Reported lesion symptoms include bothersome appearance; the patient considered this a rash; the leg is involved; no relevant systemic symptoms; the subject is 18–29, female; this image was taken at an angle; the patient reports the condition has been present for about one day — 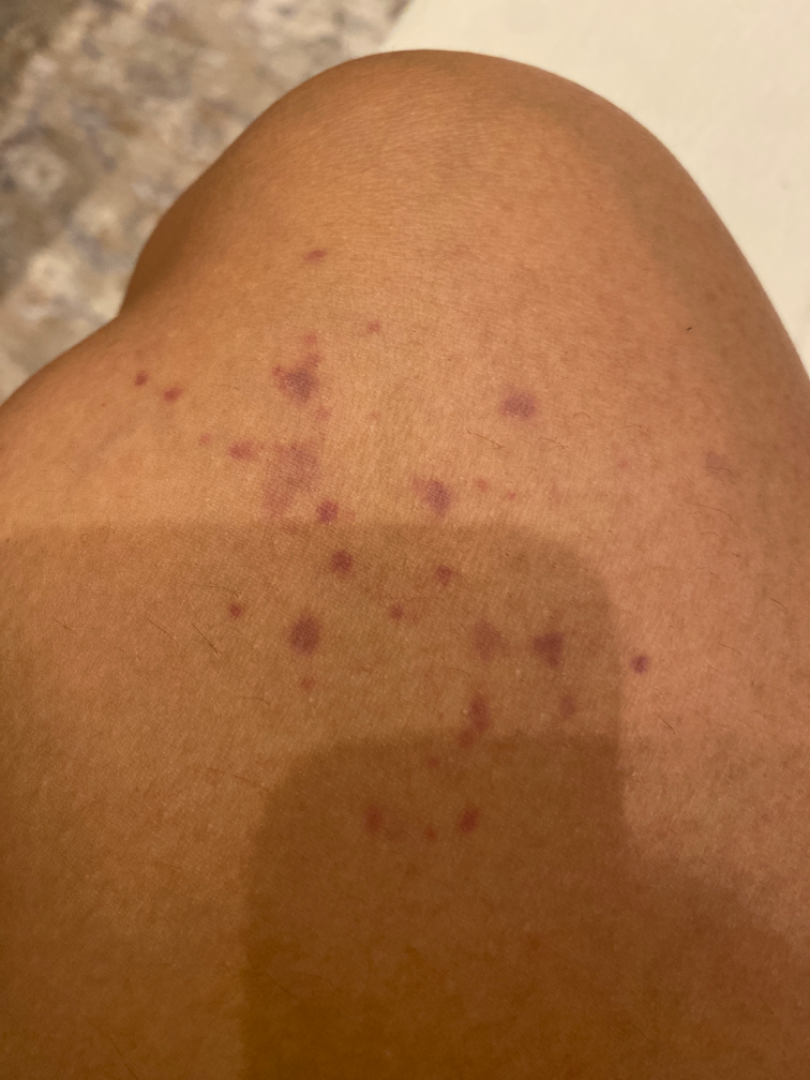assessment: could not be assessed